A close-up photograph: 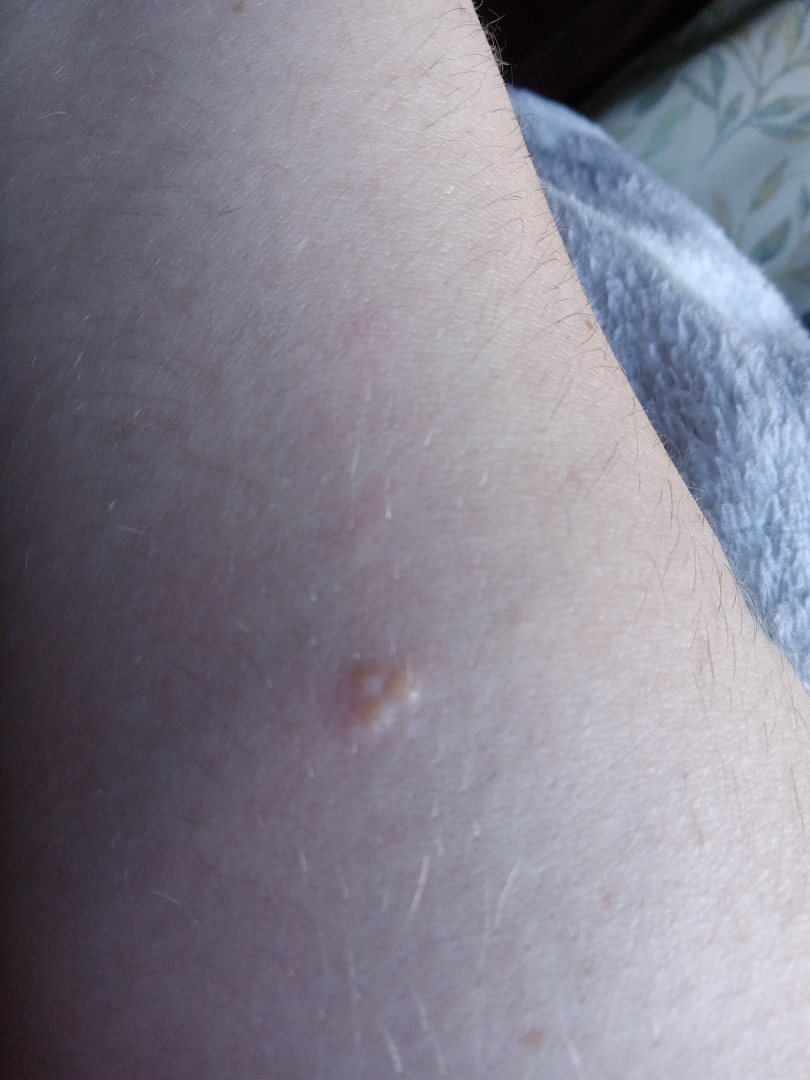{"differential": {"tied_lead": ["Verruca vulgaris", "Molluscum Contagiosum", "Allergic Contact Dermatitis"]}}